Close-up view, the affected area is the leg.
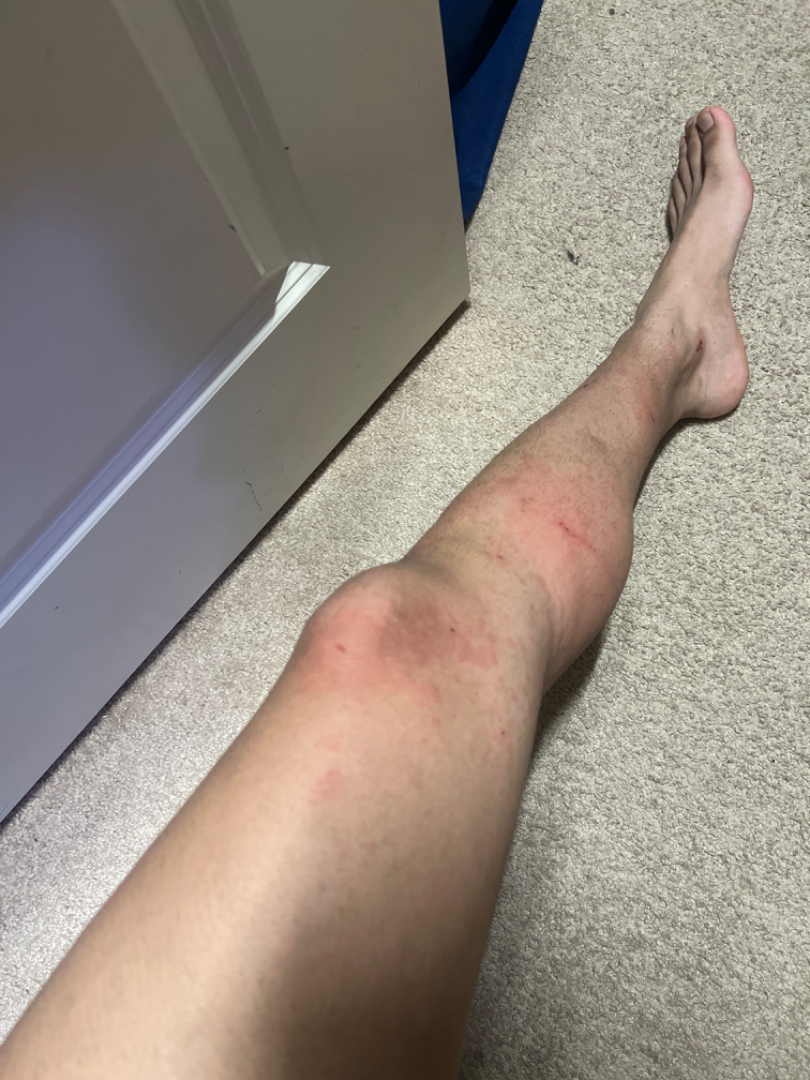described texture: raised or bumpy, symptom duration: less than one week, patient describes the issue as: a rash, systemic symptoms: none reported, symptoms: itching and enlargement, clinical impression: most consistent with Urticaria; also on the differential is Allergic Contact Dermatitis.